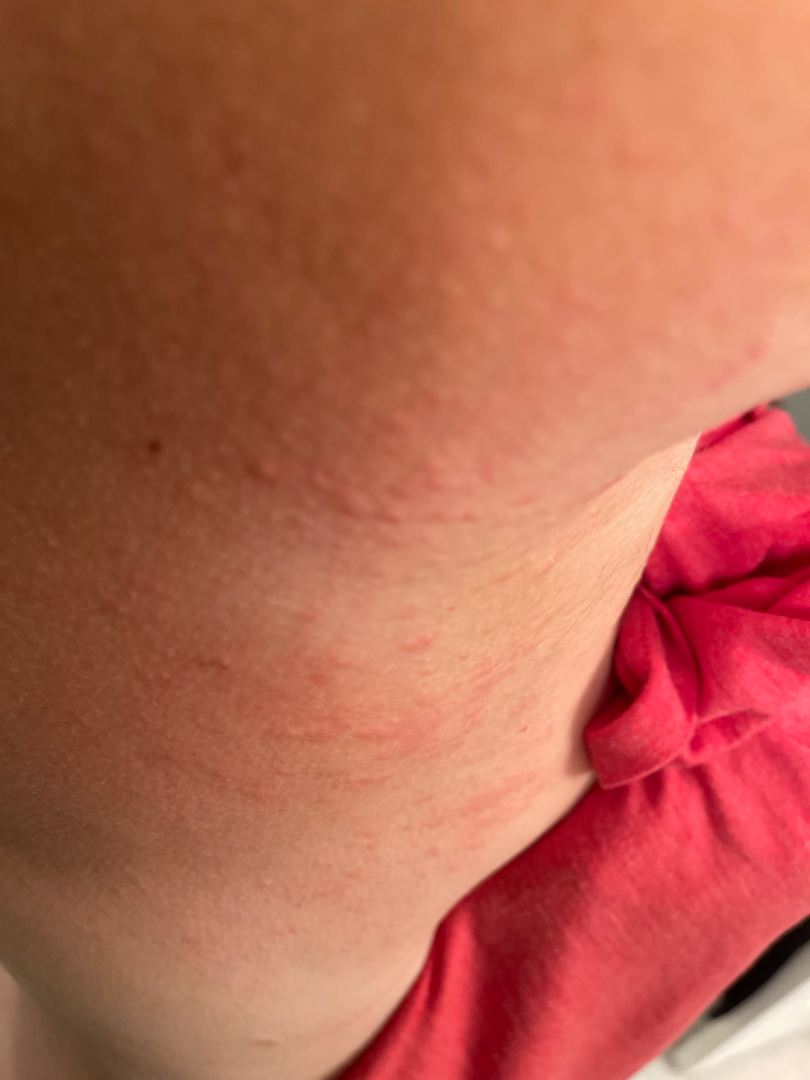differential:
  leading:
    - Allergic Contact Dermatitis
  considered:
    - Eczema
  unlikely:
    - Folliculitis